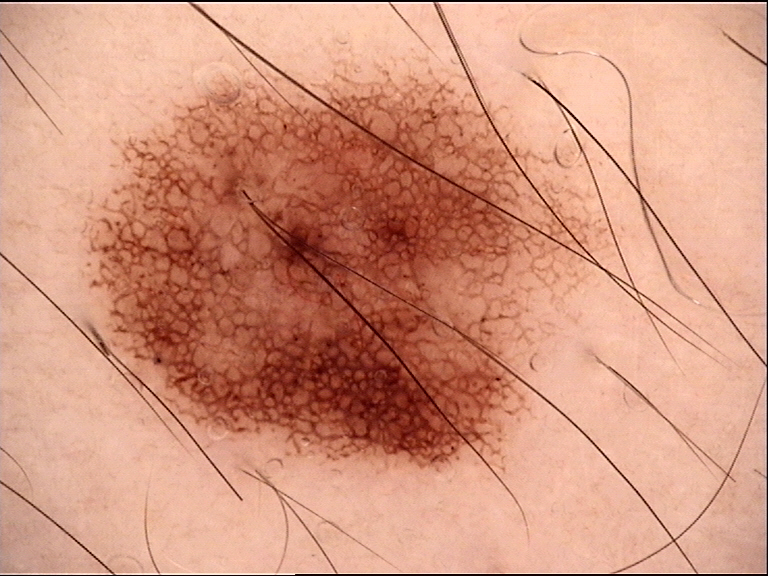– class · dysplastic junctional nevus (expert consensus)